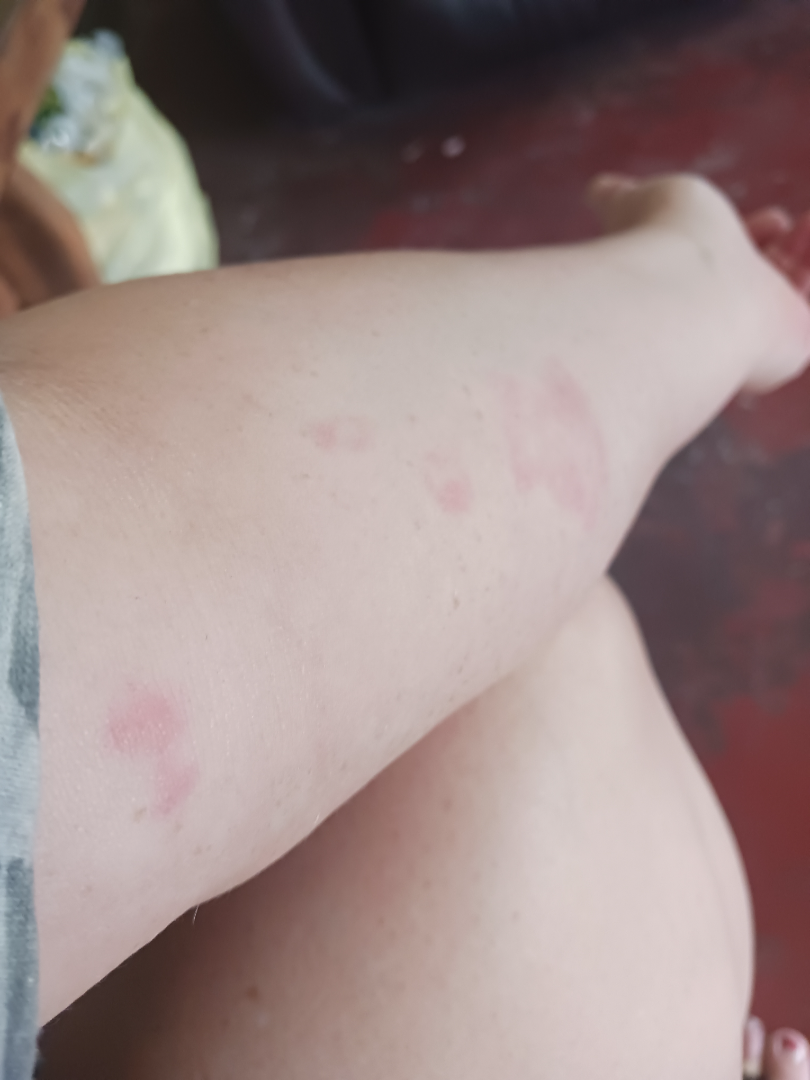The reviewing dermatologist was unable to assign a differential diagnosis from the image. The photo was captured at an angle. The subject is a female aged 40–49. Located on the arm.